By self-report, a personal history of skin cancer and a personal history of cancer. Few moles overall by the patient's own estimate. A male subject age 76. A dermoscopic image of a skin lesion. Collected as part of a research study, without a referral diagnosis. The patient says their skin reddens with sun exposure — 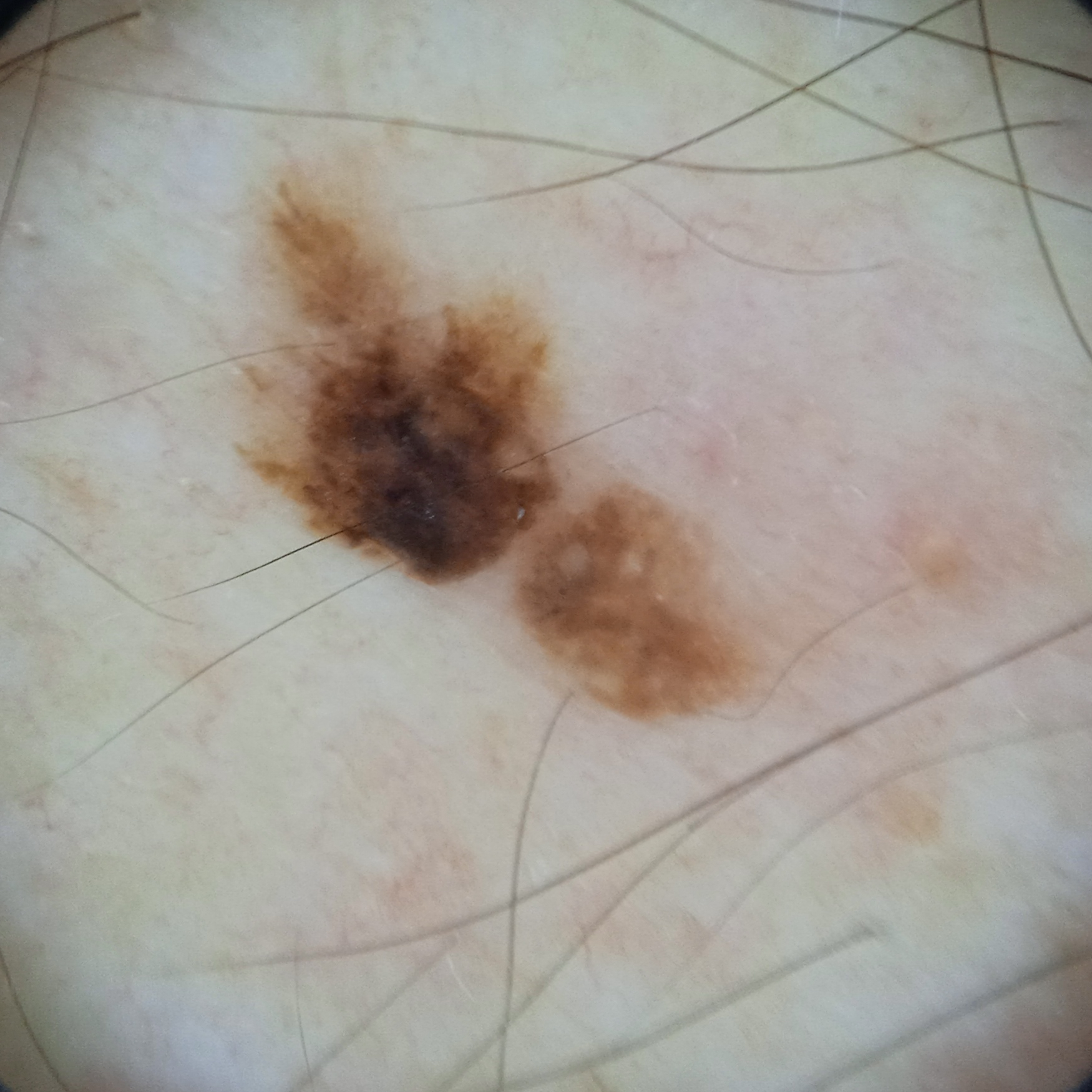site: the back | diameter: 7.8 mm | diagnosis: seborrheic keratosis (dermatologist consensus).